Dermoscopy of a skin lesion.
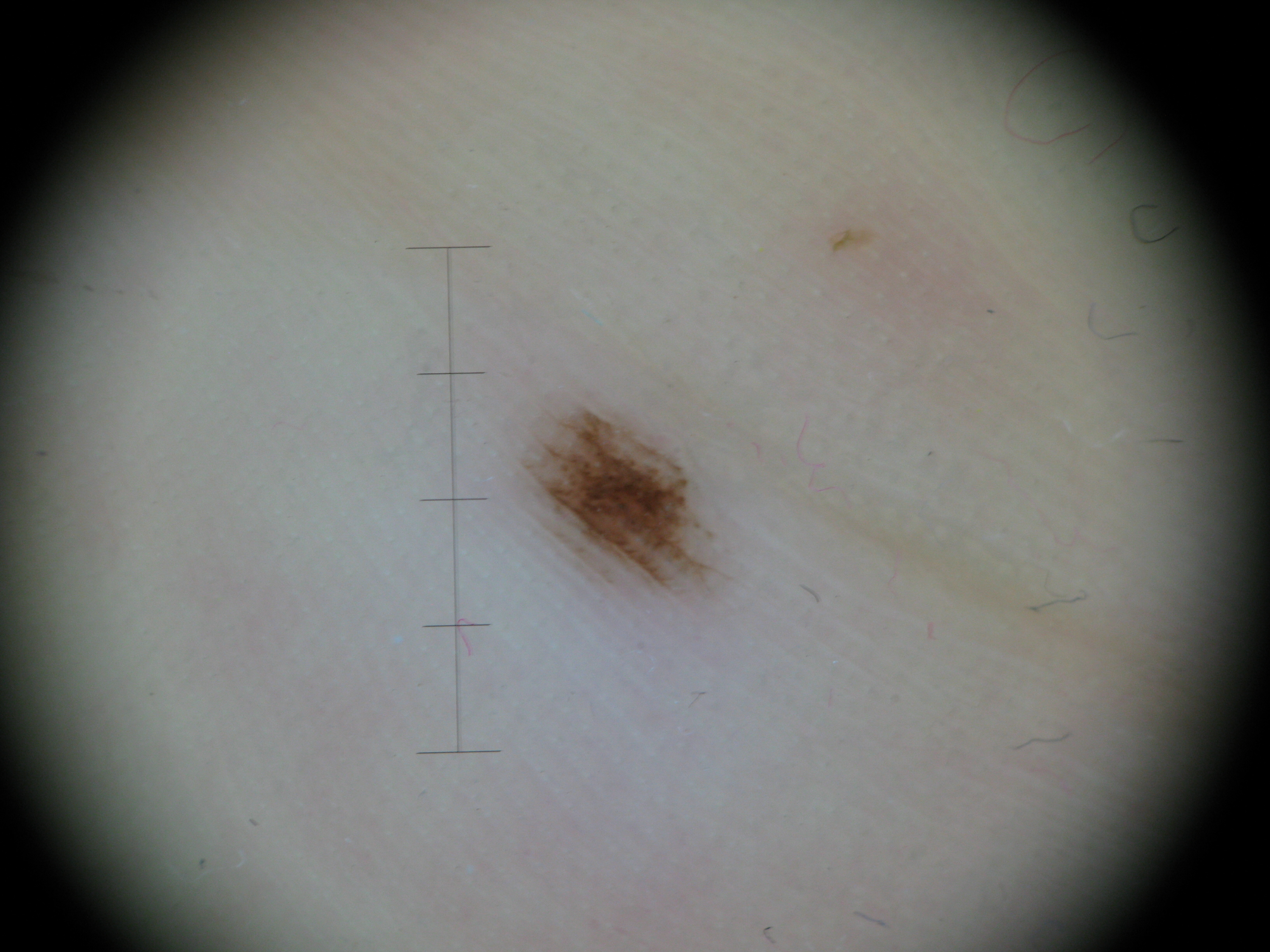- assessment: acral junctional nevus (expert consensus)